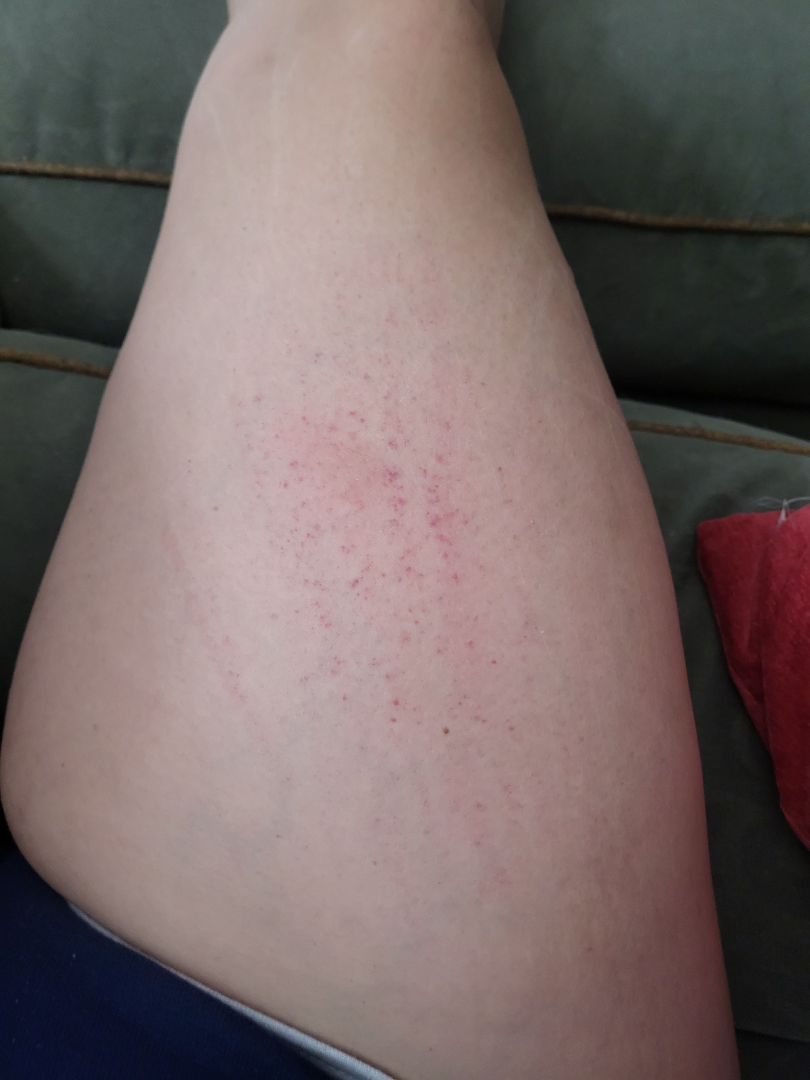history=about one day
body site=leg
photo taken=at a distance
symptoms=itching
texture=flat
dermatologist impression=the leading consideration is Traumatic petechiae